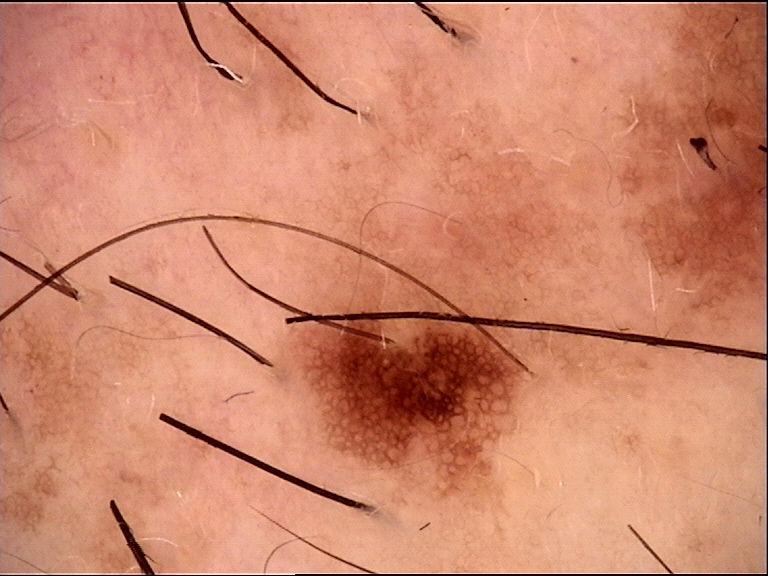Q: What is the imaging modality?
A: dermoscopy
Q: What is this lesion?
A: dysplastic junctional nevus (expert consensus)